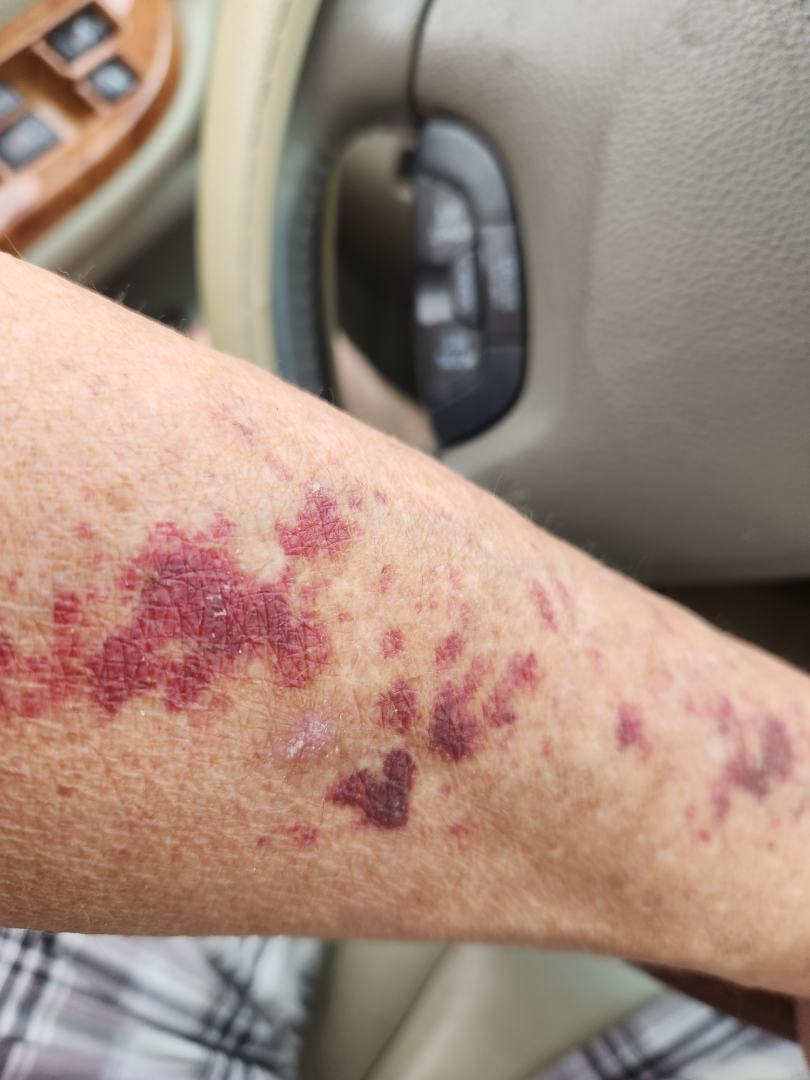Clinical context:
This is a close-up image.
Assessment:
On photographic review: the impression is ecchymoses.